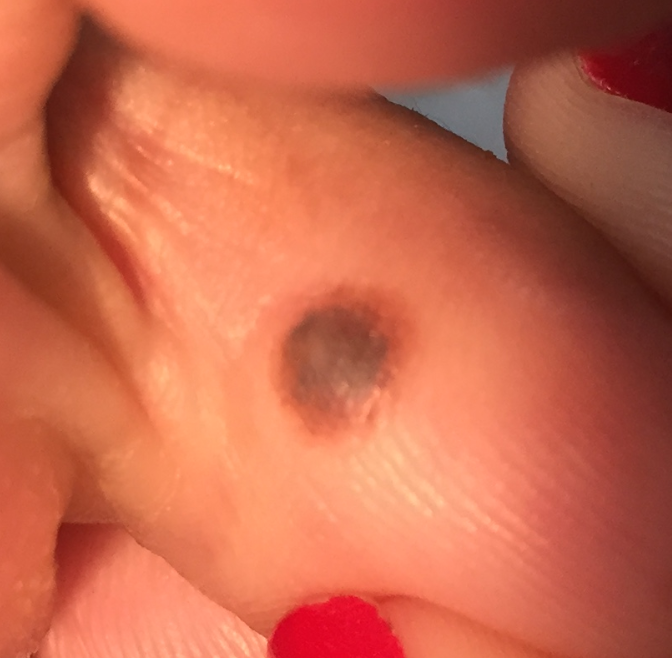A subject 58 years of age.
Located on a foot.
By the patient's account, the lesion is elevated, but does not hurt.
Diagnosed by dermatologist consensus as a nevus.